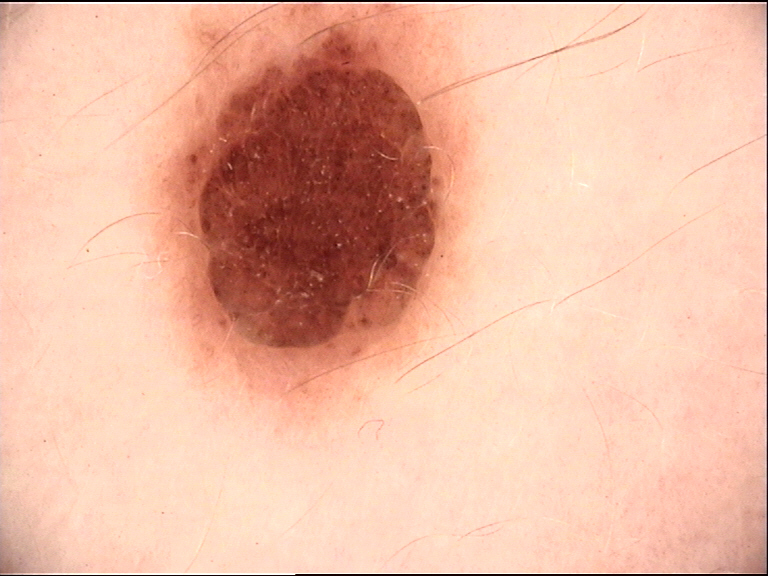image: dermatoscopy | diagnostic label: dermal nevus (expert consensus).